A dermoscopic image of a skin lesion.
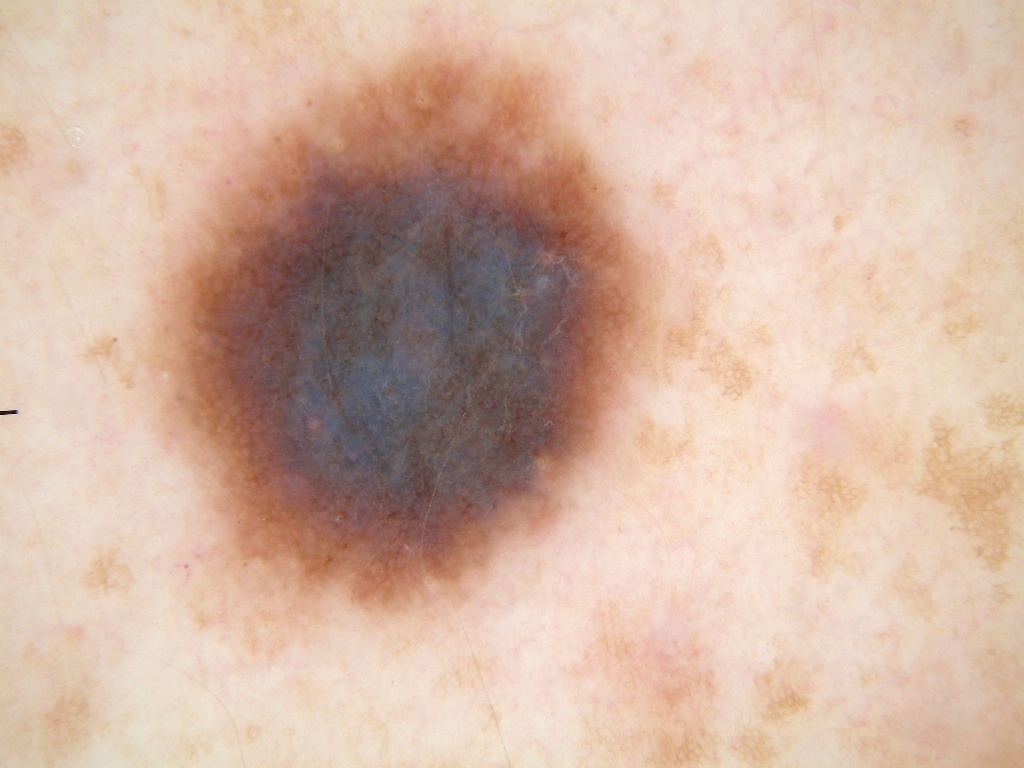location=143, 47, 652, 615 | features=pigment network | diagnostic label=a melanocytic nevus.